A male patient 76 years of age; the patient says their skin reddens with sun exposure.
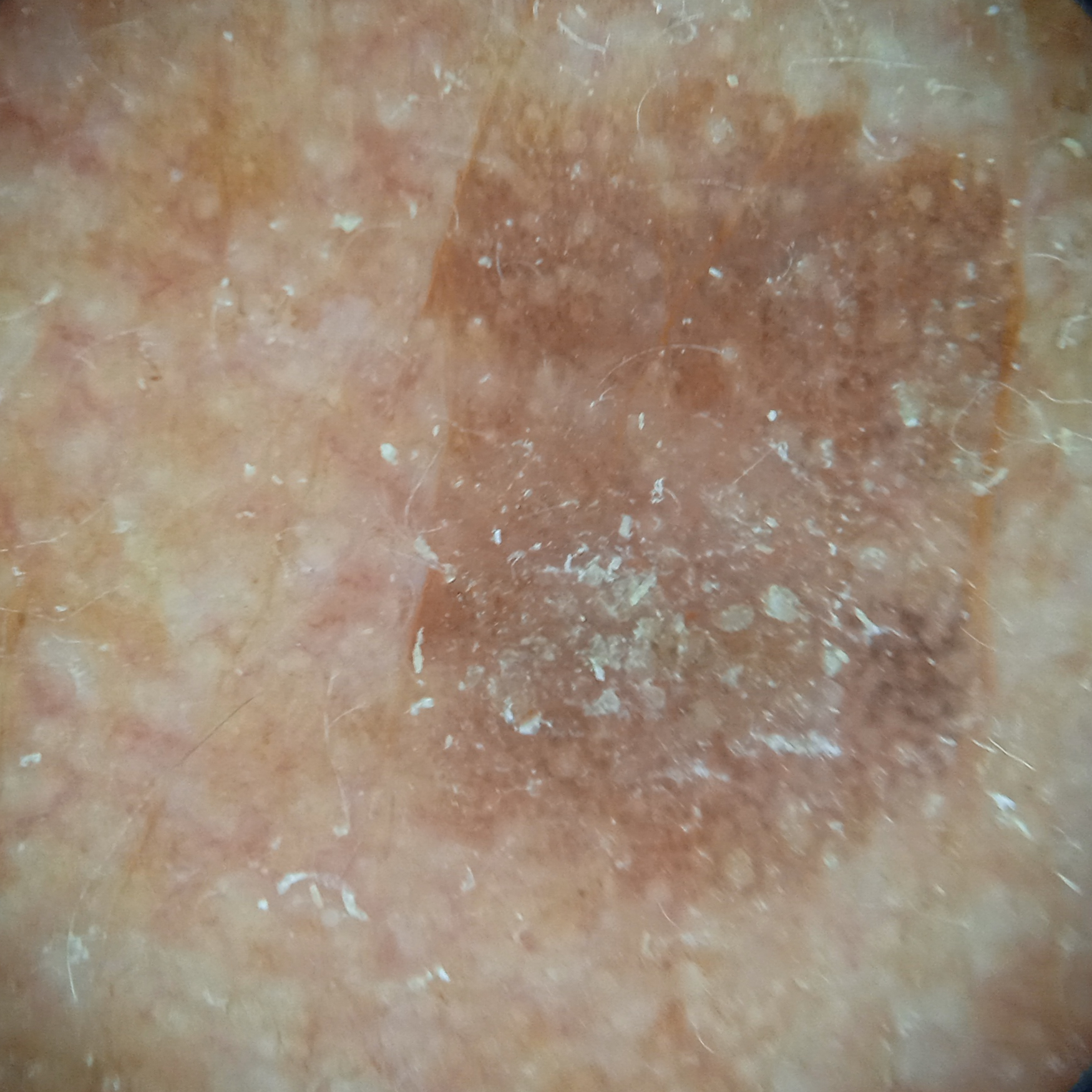The lesion involves the face. The biopsy diagnosis was a basal cell carcinoma, following excision, with tumor thickness 2.5 mm.